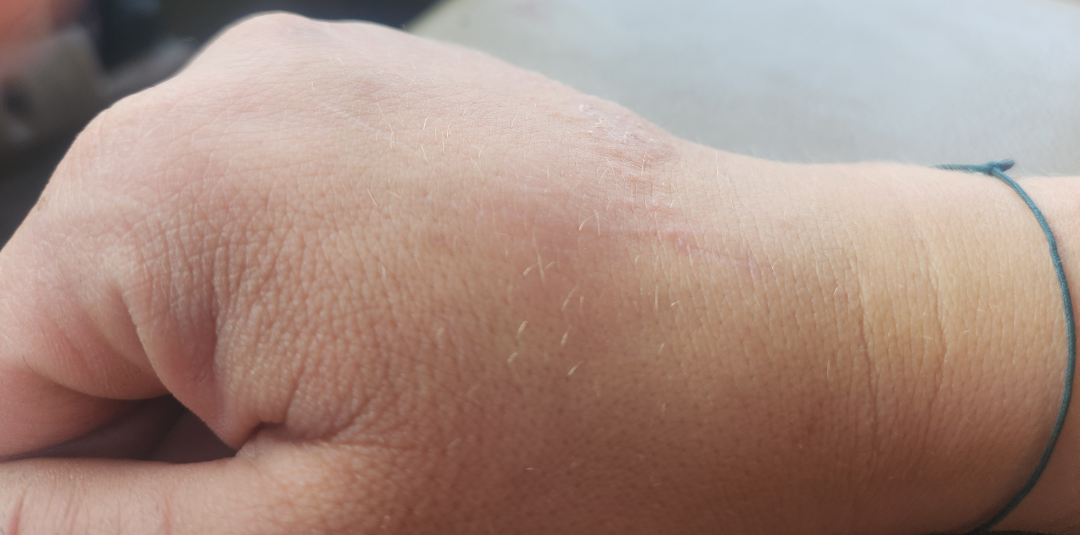Case summary:
* assessment — Eczema (primary); Irritant Contact Dermatitis (considered); Allergic Contact Dermatitis (unlikely)